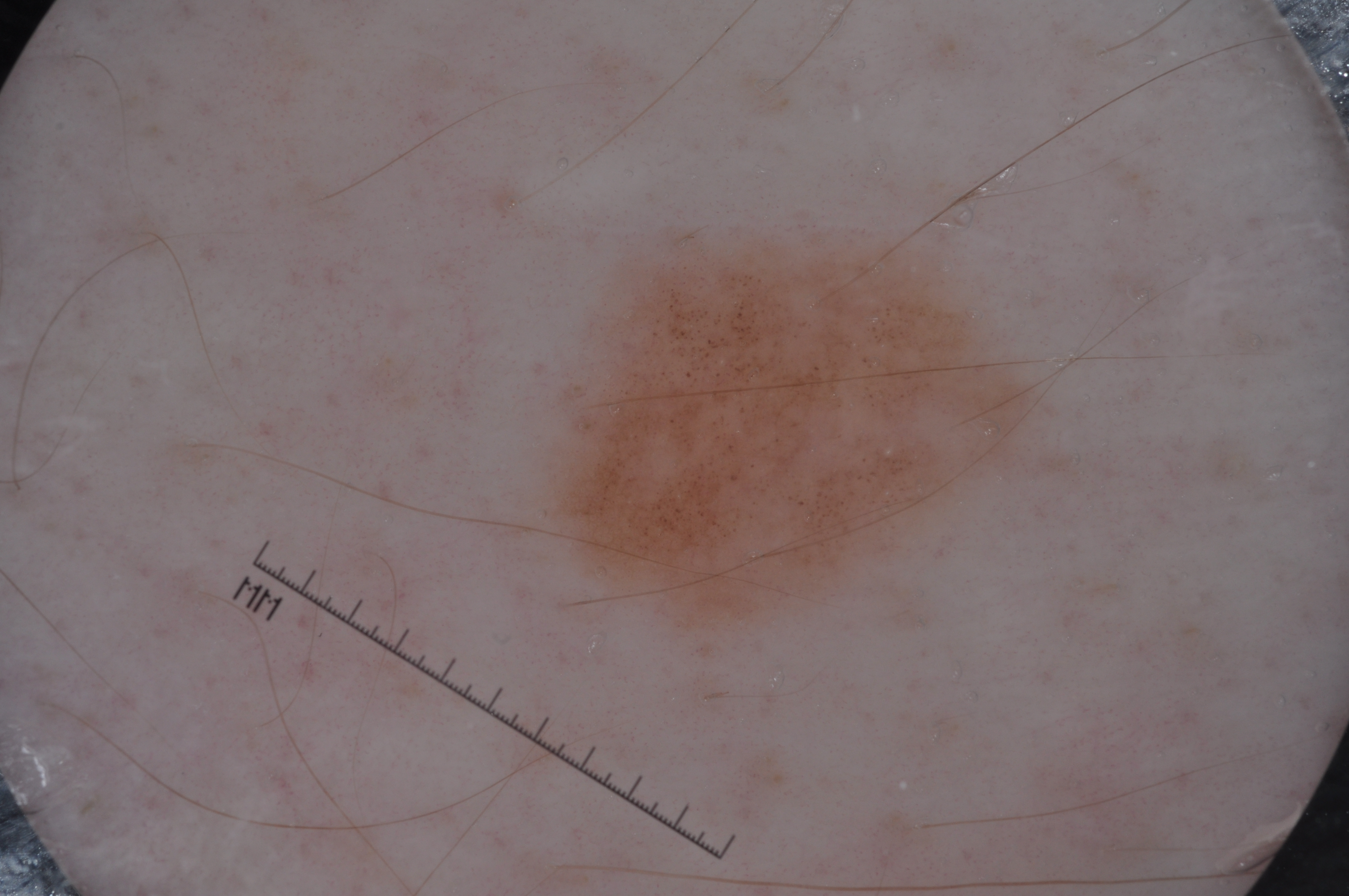Q: What kind of image is this?
A: dermoscopy
Q: Patient demographics?
A: male, approximately 55 years of age
Q: How much of the field does the lesion occupy?
A: ~11% of the field
Q: What dermoscopic features are present?
A: milia-like cysts and pigment network
Q: What is the lesion's bounding box?
A: 548/245/1033/630
Q: What is the diagnosis?
A: a melanocytic nevus, a benign skin lesion